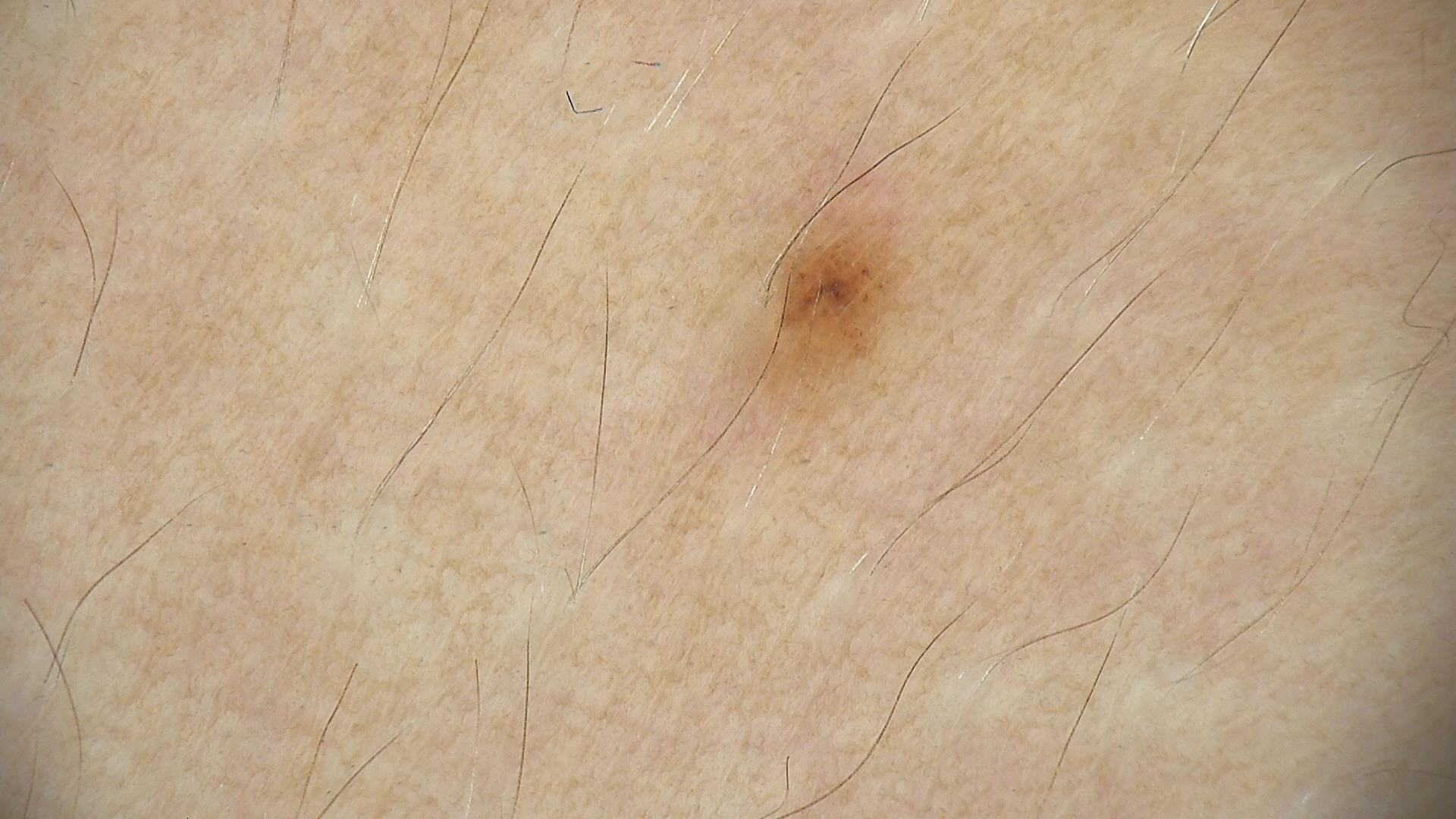Dermoscopy of a skin lesion. The diagnosis was a benign lesion — a dysplastic junctional nevus.